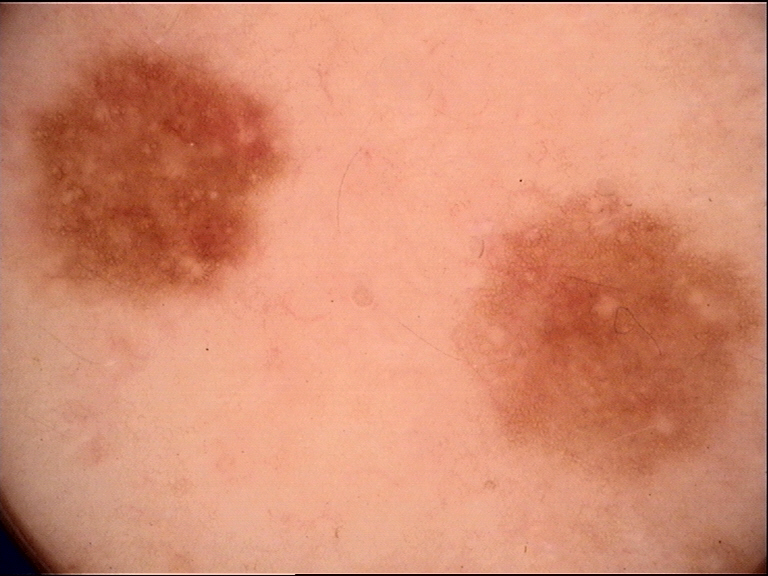modality: dermatoscopy; class: dysplastic junctional nevus (expert consensus).